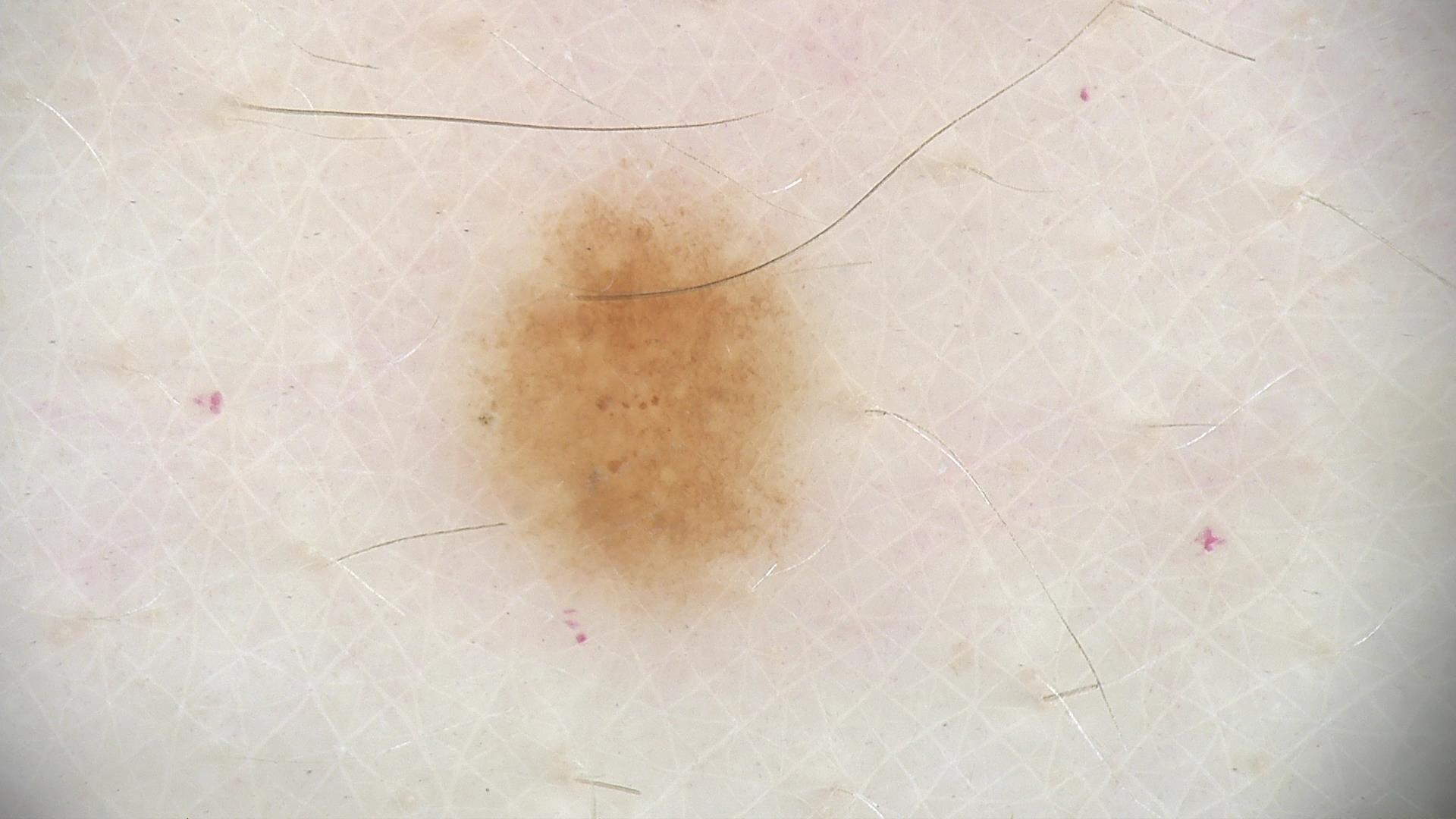The diagnosis was a dysplastic junctional nevus.